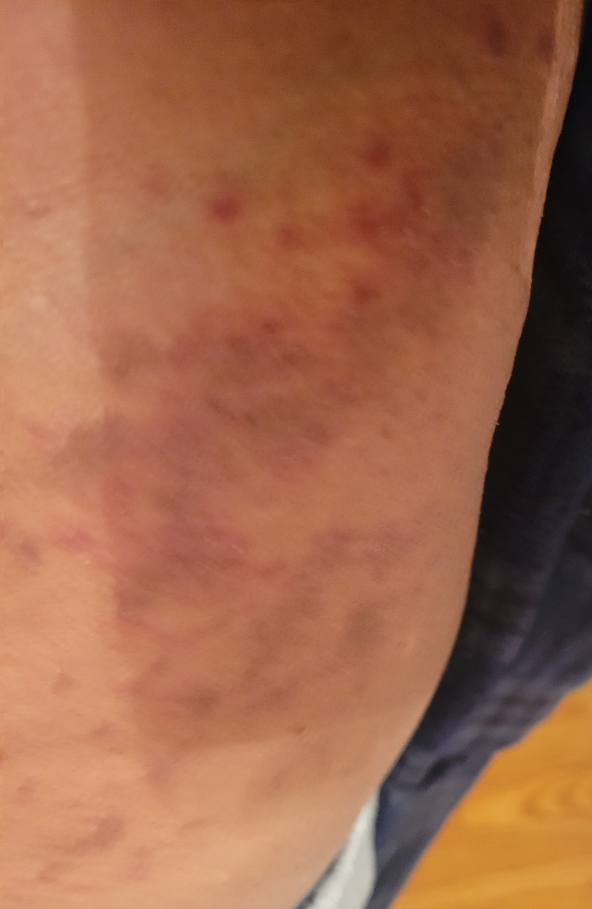  assessment: not assessable